The photograph is a close-up of the affected area · located on the arm.
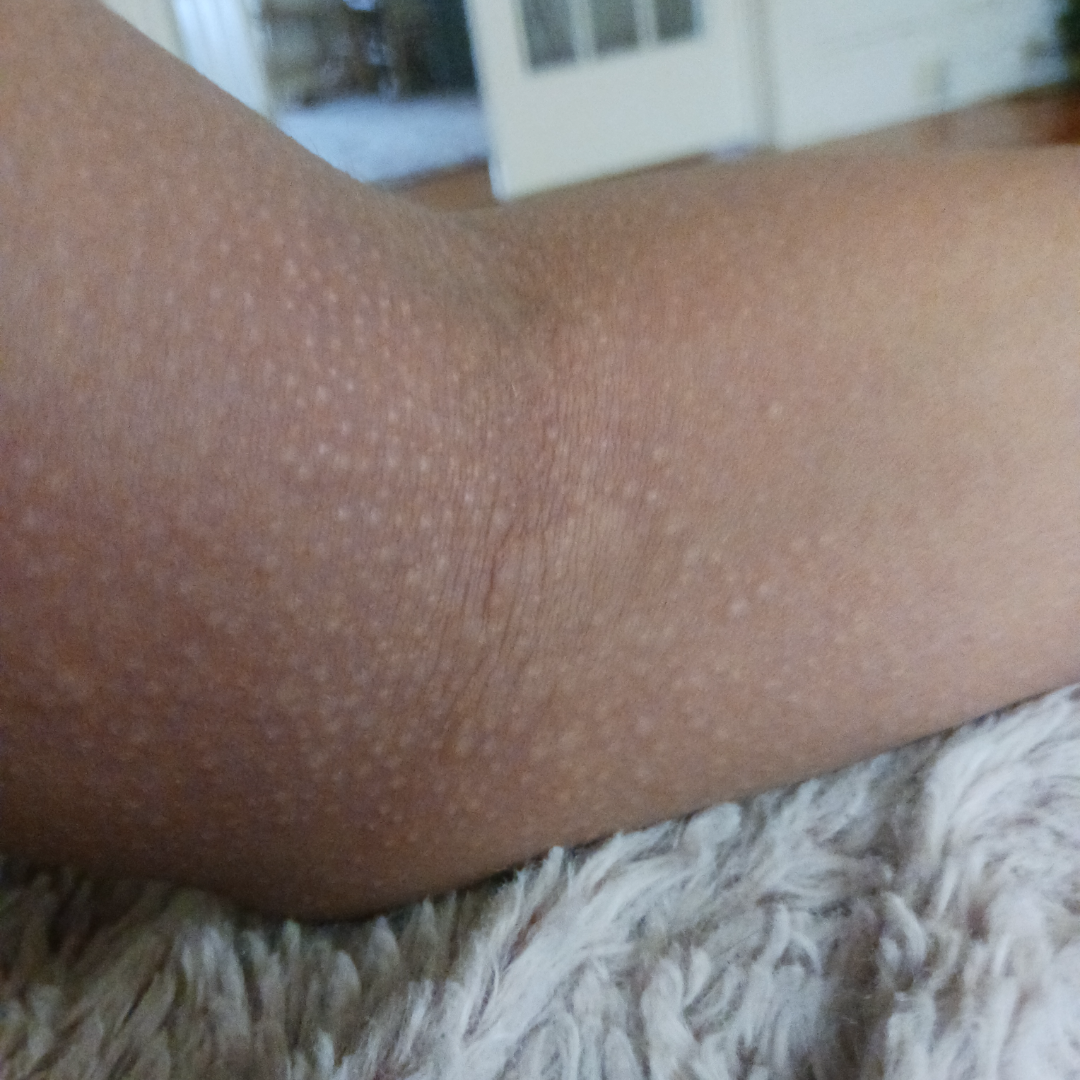other reported symptoms: none reported | surface texture: raised or bumpy | patient describes the issue as: a rash | differential: the leading consideration is Eczema; less likely is Lichen nitidus; less probable is Urticaria; lower on the differential is Allergic Contact Dermatitis.